The patient considered this a rash; the patient reports the lesion is raised or bumpy; Fitzpatrick phototype III; the condition has been present for less than one week; close-up view; female patient, age 40–49; the lesion involves the back of the torso, arm, head or neck and front of the torso; the patient reports associated fatigue; symptoms reported: itching:
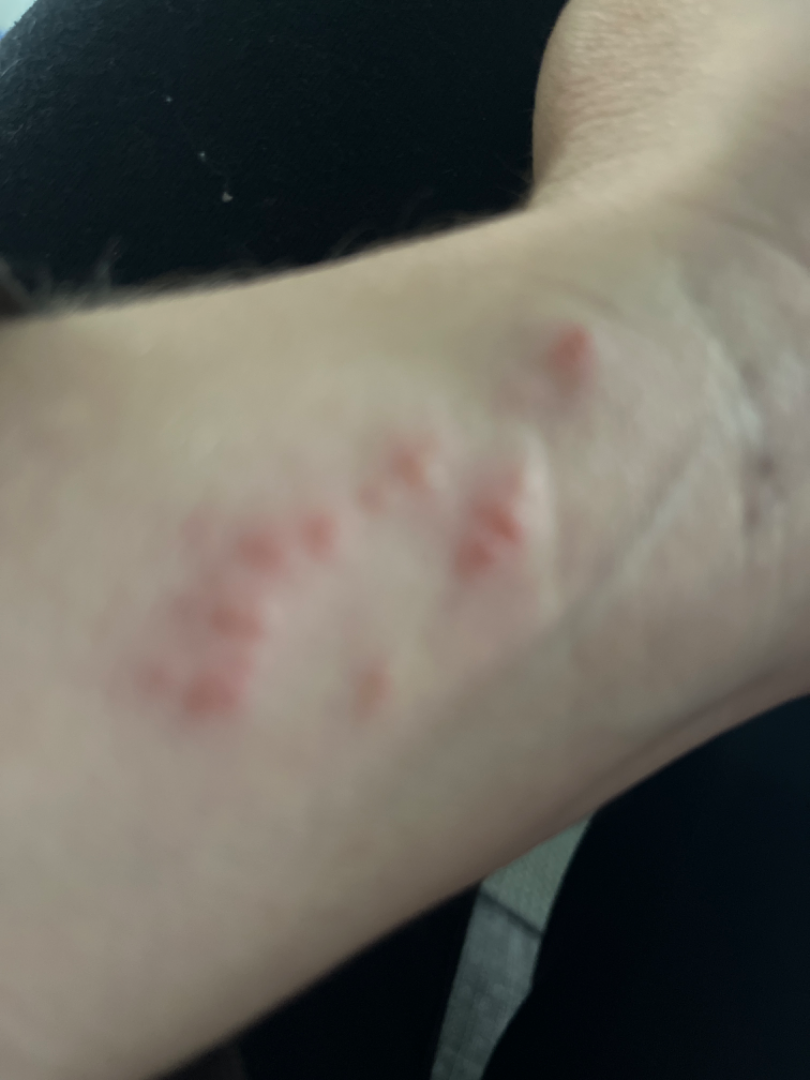The case was difficult to assess from the available photograph.